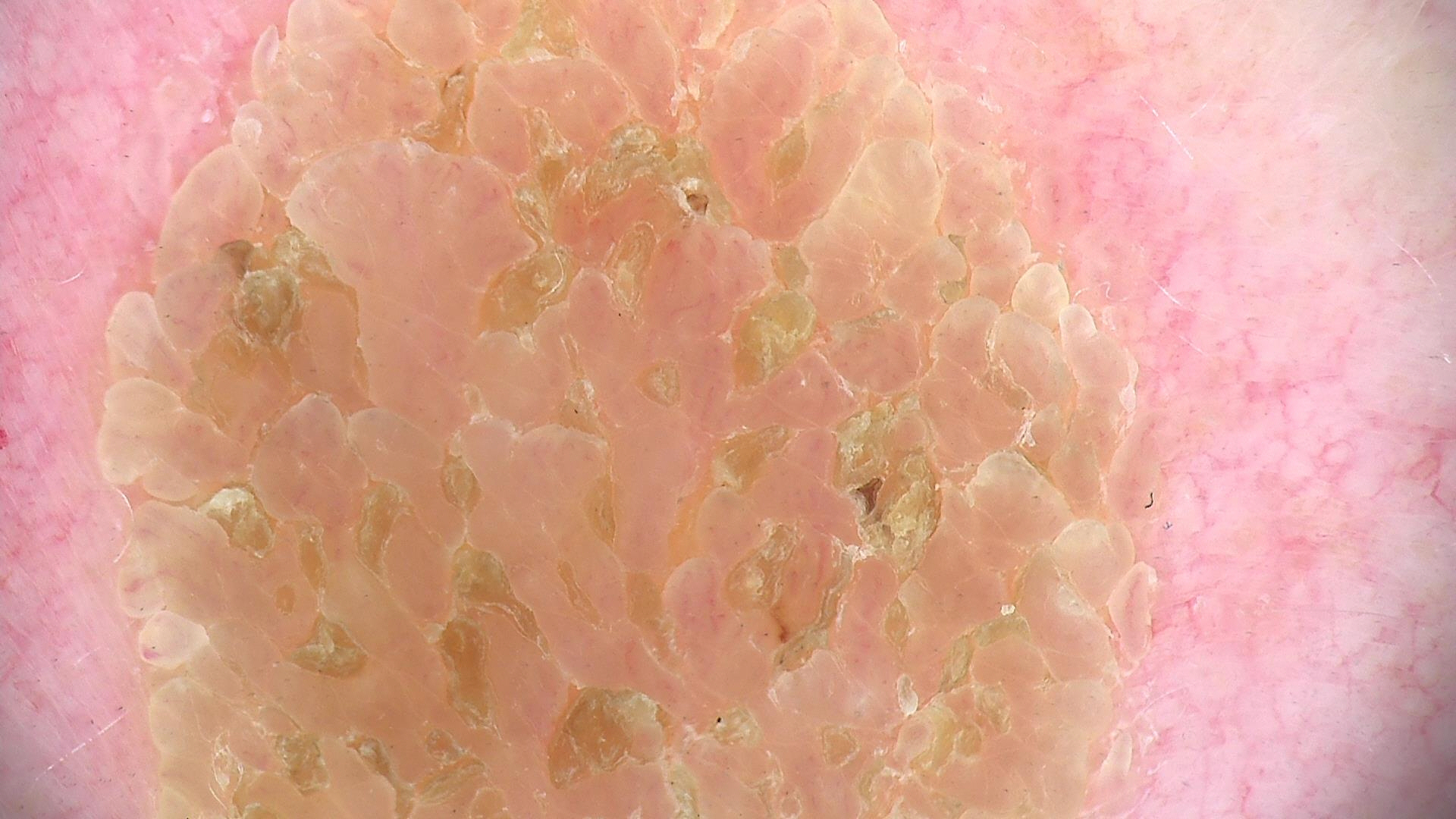Conclusion: Diagnosed as a dermal nevus.